Dermoscopy of a skin lesion.
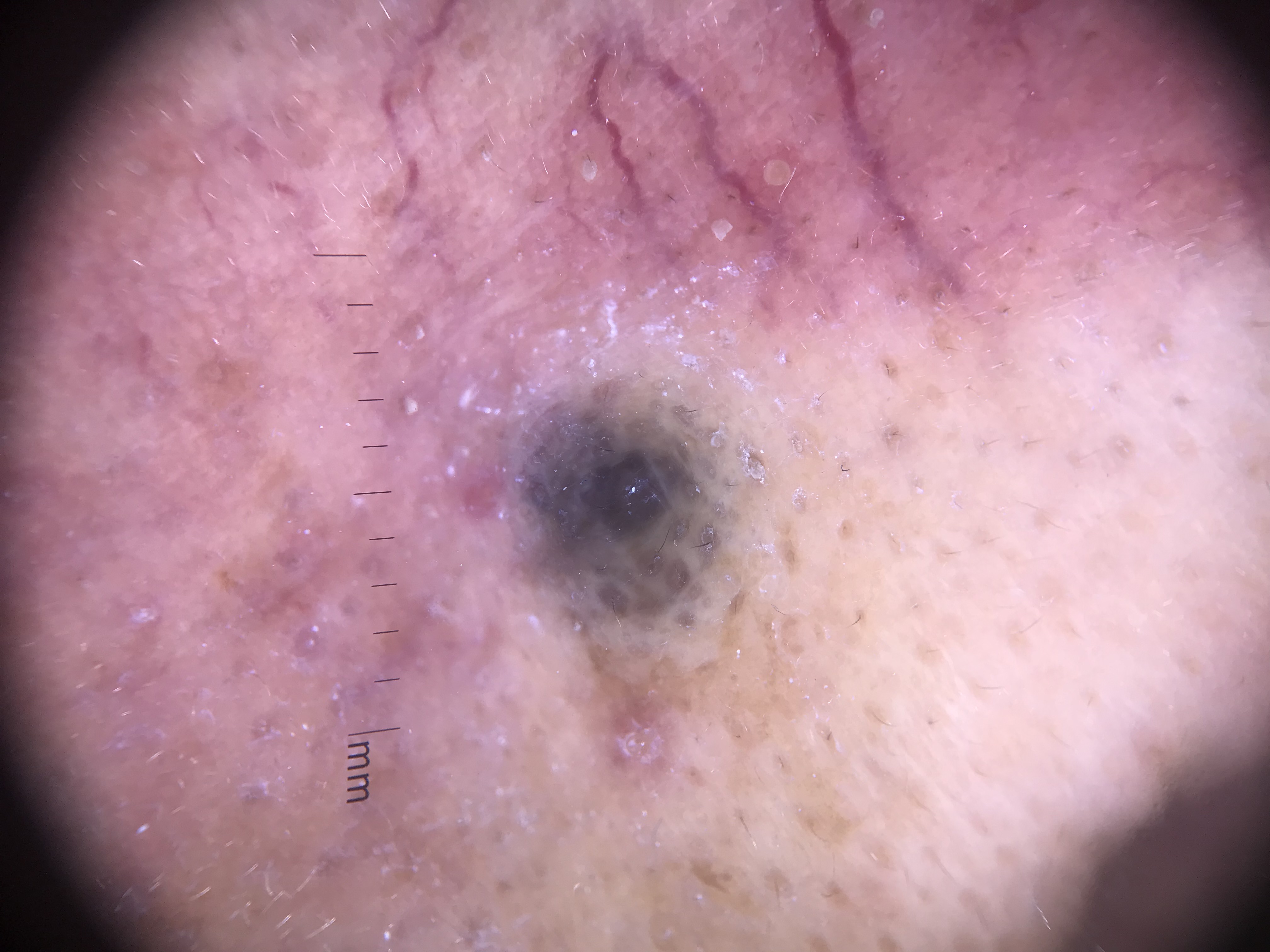{
  "lesion_type": {
    "main_class": "banal",
    "pattern": "dermal"
  },
  "diagnosis": {
    "name": "blue nevus",
    "code": "bdb",
    "malignancy": "benign",
    "super_class": "melanocytic",
    "confirmation": "expert consensus"
  }
}